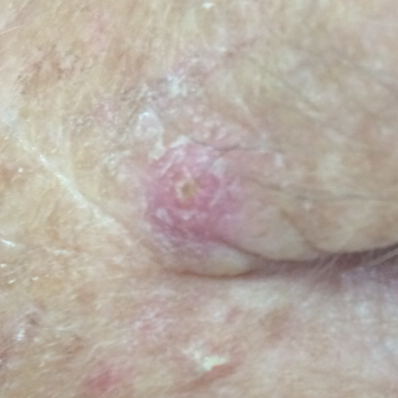| feature | finding |
|---|---|
| Fitzpatrick | III |
| risk factors | prior malignancy (patient or family) |
| lesion size | approx. 6 × 6 mm |
| symptoms | itching / no bleeding |
| diagnostic label | actinic keratosis (biopsy-proven) |